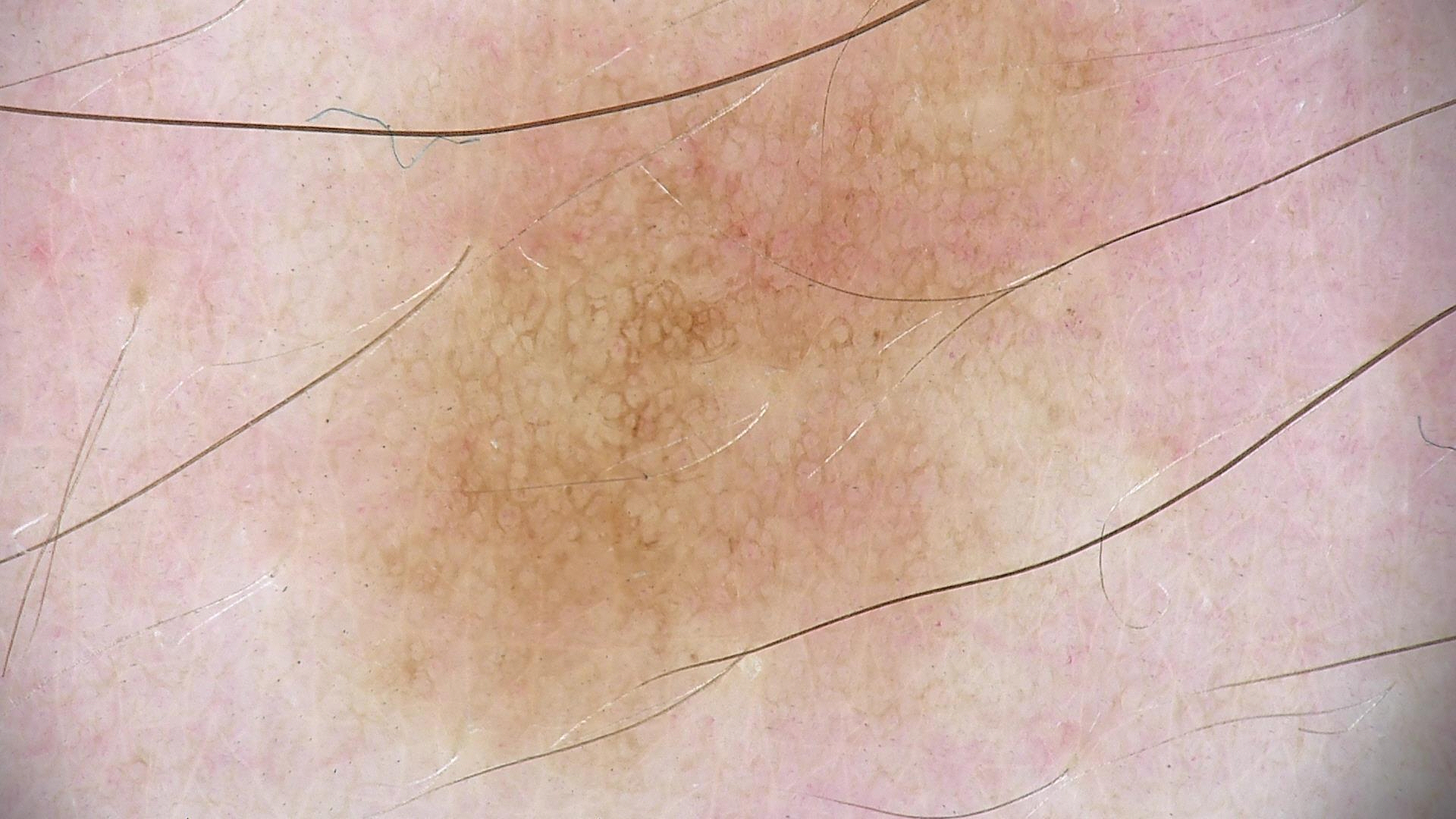diagnostic label = dysplastic junctional nevus (expert consensus)